A dermatoscopic image of a skin lesion:
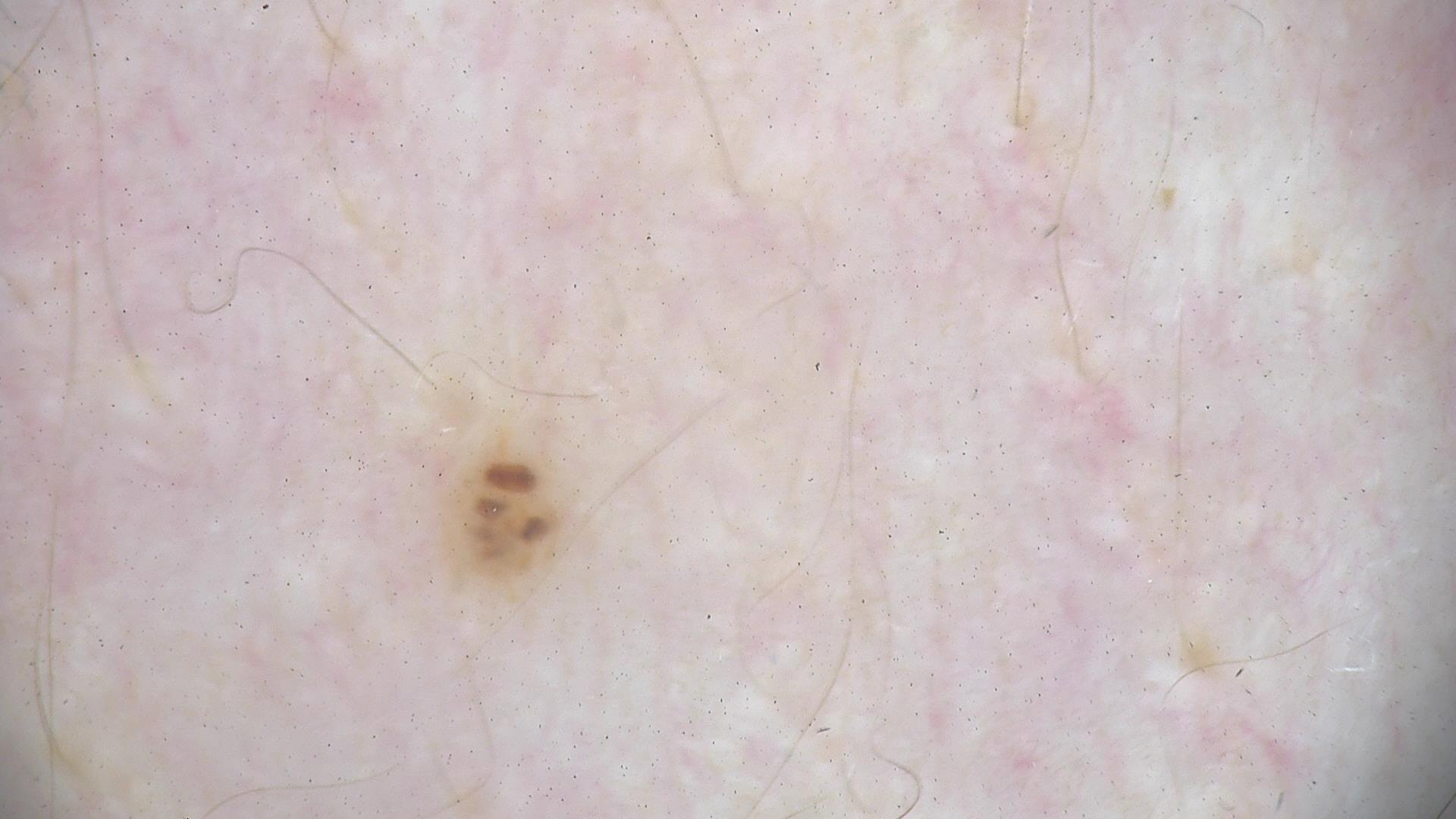Diagnosed as a benign lesion — a dysplastic junctional nevus.